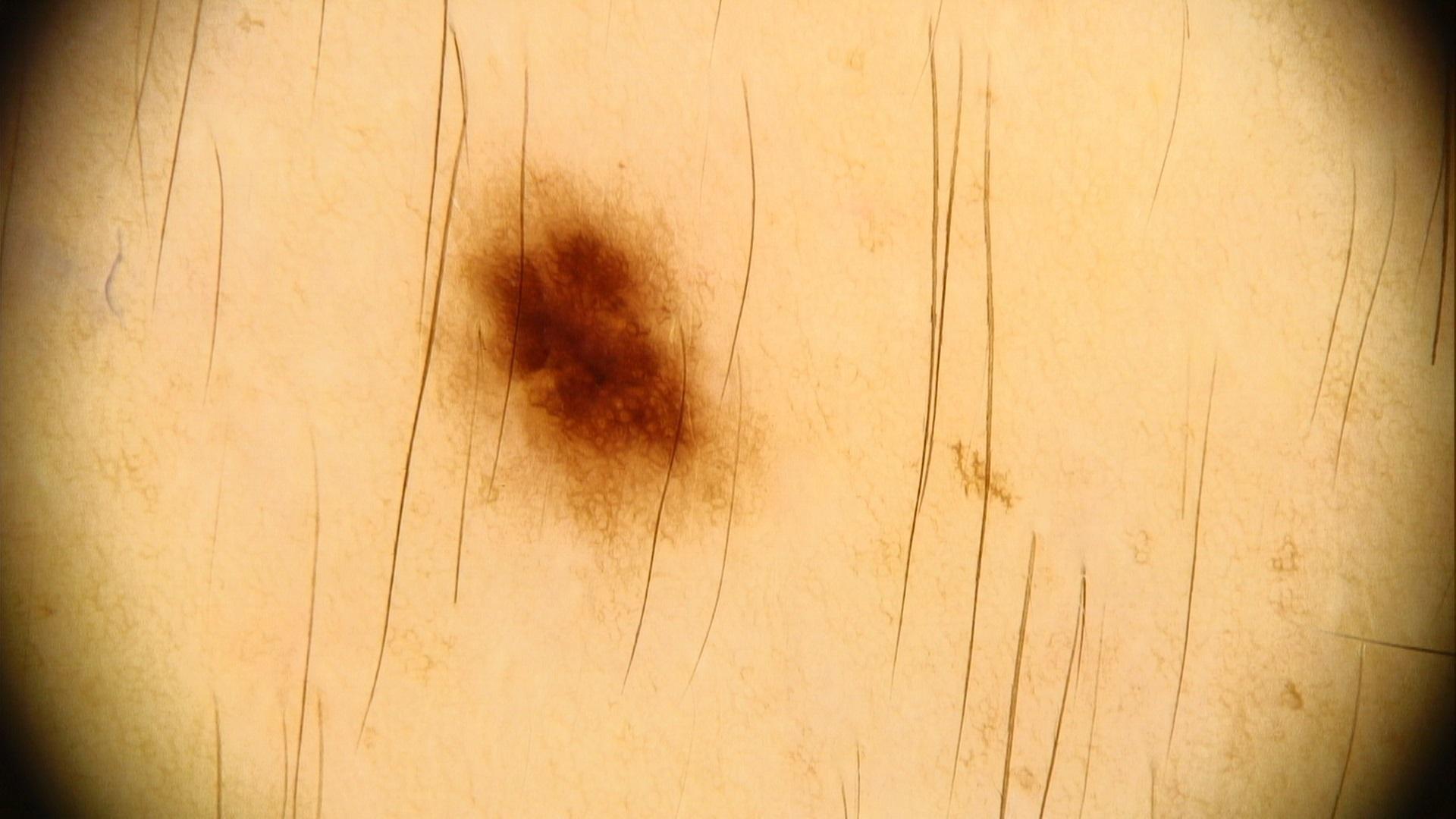| field | value |
|---|---|
| FST | III |
| imaging | dermoscopy |
| patient | male, aged 38-42 |
| site | the trunk, specifically the posterior trunk |
| diagnosis | Nevus (clinical impression) |